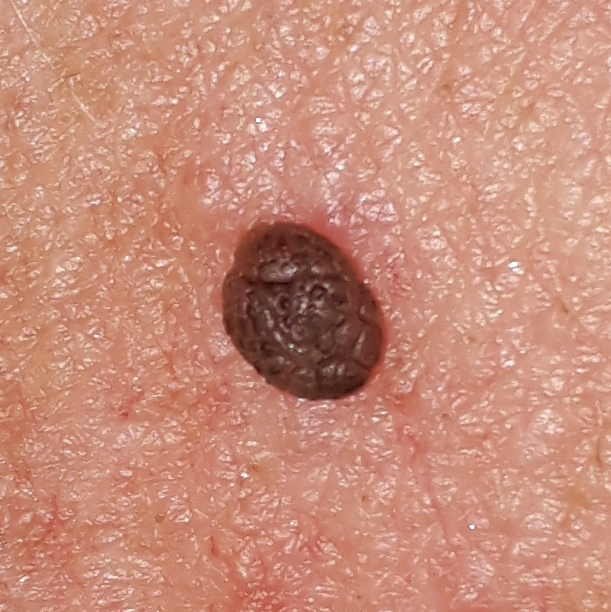subject: age 55 | image: clinical photo | region: the chest | reported symptoms: bleeding, elevation / no itching | impression: seborrheic keratosis (clinical consensus).